This is a dermoscopic photograph of a skin lesion — 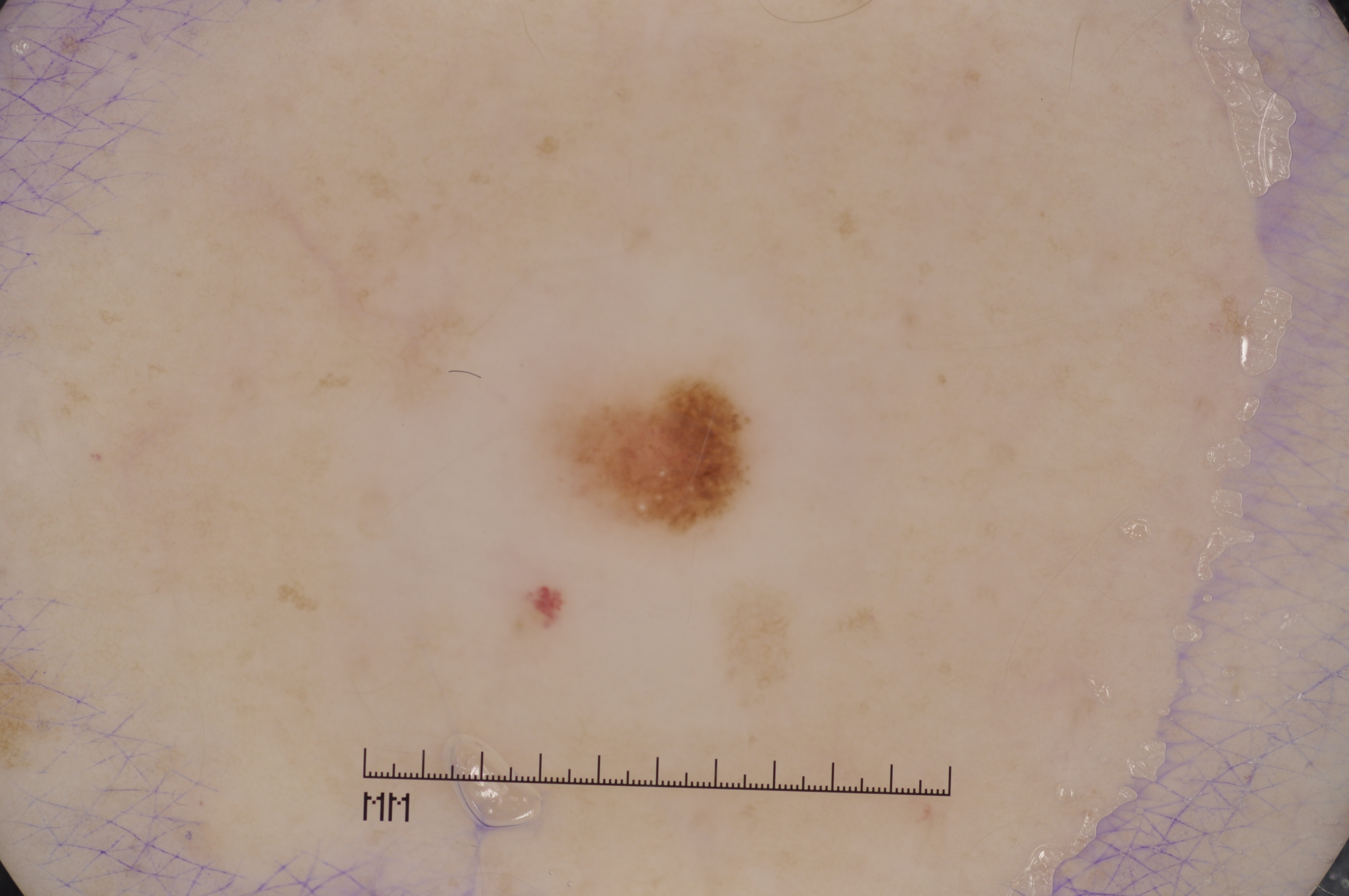| feature | finding |
|---|---|
| location | bbox=[548, 378, 748, 532] |
| dermoscopic findings | pigment network and milia-like cysts |
| diagnostic label | a melanocytic nevus, a benign skin lesion |